The affected area is the leg; close-up view — 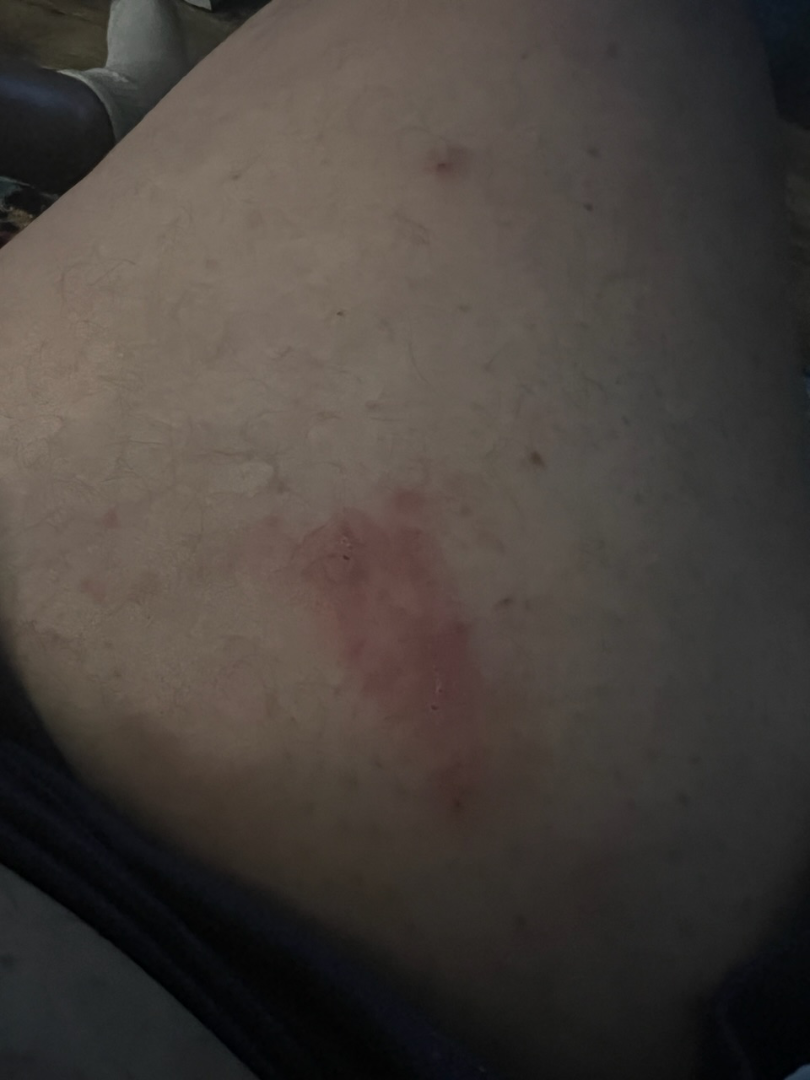Assessment:
The reviewer was unable to grade this case for skin condition.
Clinical context:
Symptoms reported: enlargement and itching. Non-clinician graders estimated MST 2 or 3 (two reviewer pools). The lesion is described as raised or bumpy. Self-categorized by the patient as a rash.